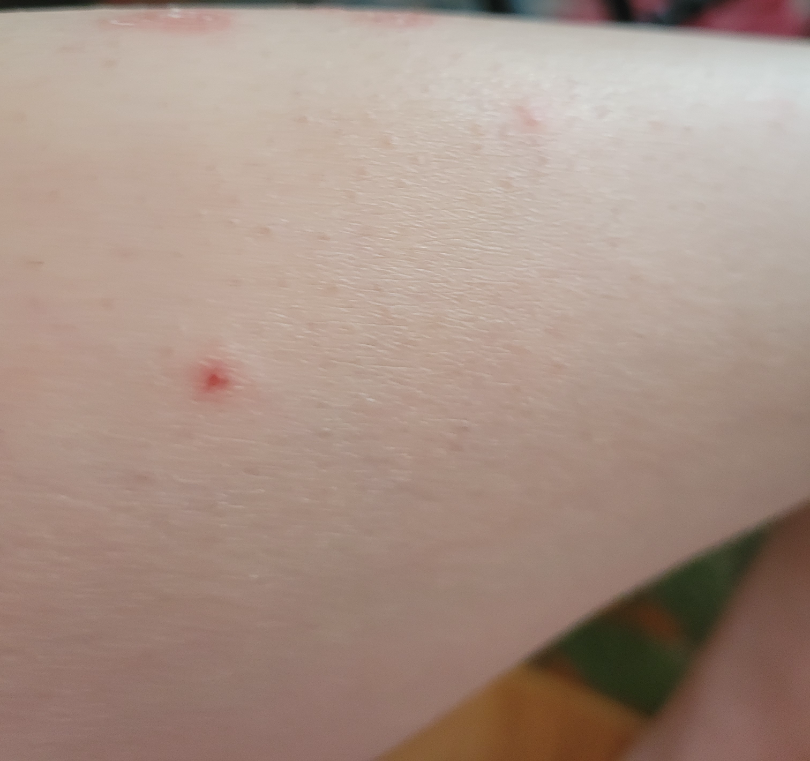<dermatology_case>
  <skin_tone>
    <monk_skin_tone>2, 3</monk_skin_tone>
  </skin_tone>
  <body_site>leg</body_site>
  <patient>female, age 30–39</patient>
  <texture>rough or flaky, raised or bumpy</texture>
  <shot_type>at an angle</shot_type>
  <symptoms>bothersome appearance, itching</symptoms>
  <differential>
    <leading>Psoriasis</leading>
    <unlikely>Eczema, Drug Rash, Pityriasis lichenoides, Lichen planus/lichenoid eruption</unlikely>
  </differential>
</dermatology_case>